The photo was captured at an angle:
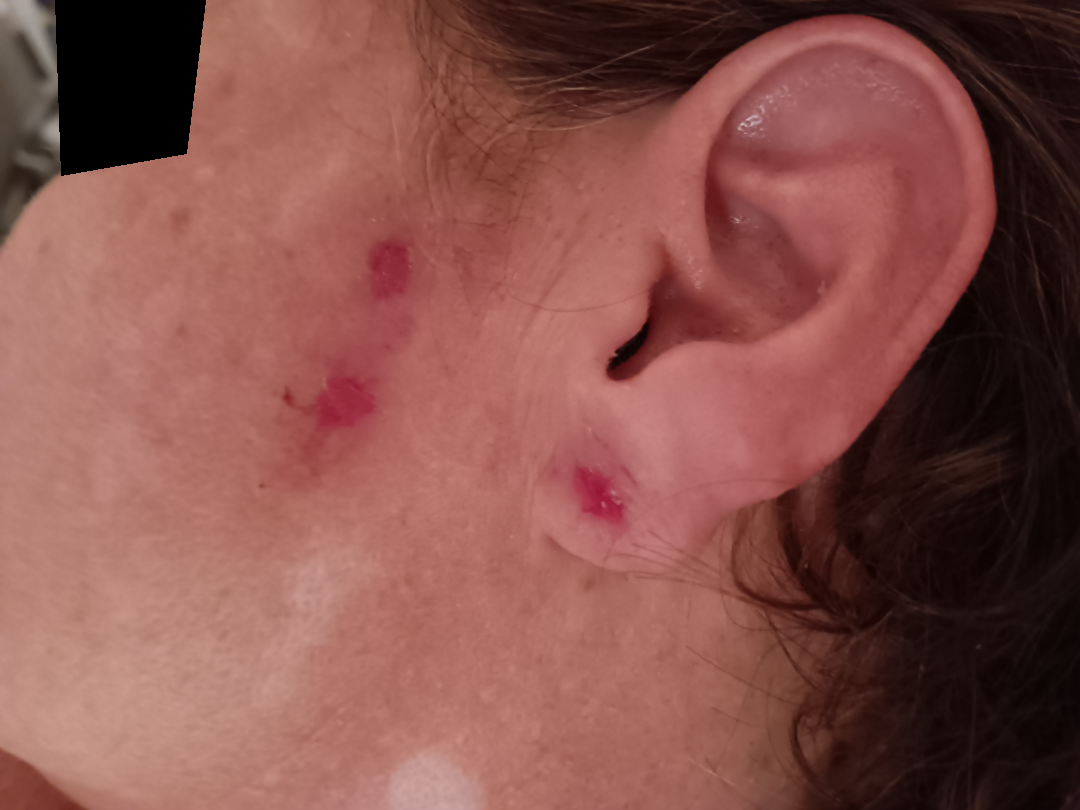| key | value |
|---|---|
| assessment | unable to determine |